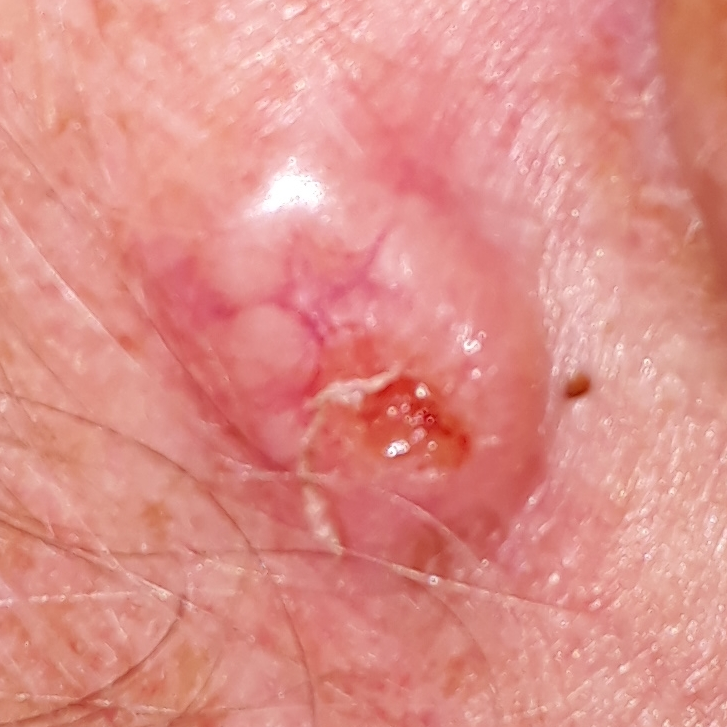<skin_lesion>
<risk_factors>
<positive>prior skin cancer (patient or family), pesticide exposure</positive>
</risk_factors>
<patient>
<age>63</age>
<gender>male</gender>
</patient>
<image>clinical photo</image>
<lesion_size>
<diameter_1_mm>10.0</diameter_1_mm>
<diameter_2_mm>8.0</diameter_2_mm>
</lesion_size>
<symptoms>
<present>growth, elevation, pain, bleeding, itching</present>
</symptoms>
<diagnosis>
<name>basal cell carcinoma</name>
<code>BCC</code>
<malignancy>malignant</malignancy>
<confirmation>histopathology</confirmation>
</diagnosis>
</skin_lesion>